A close-up photograph, the lesion is associated with enlargement and itching, the arm is involved, the subject is a female aged 60–69, the patient indicates the lesion is raised or bumpy, self-categorized by the patient as a rash: 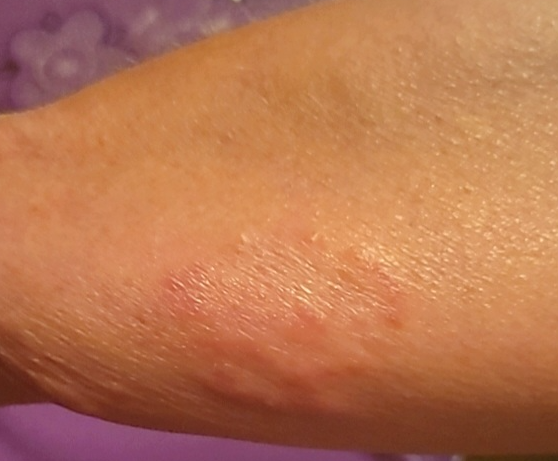Case summary:
* dermatologist impression: Granuloma annulare (leading); Erythema annulare centrifugum (considered); Cutaneous sarcoidosis (less likely)